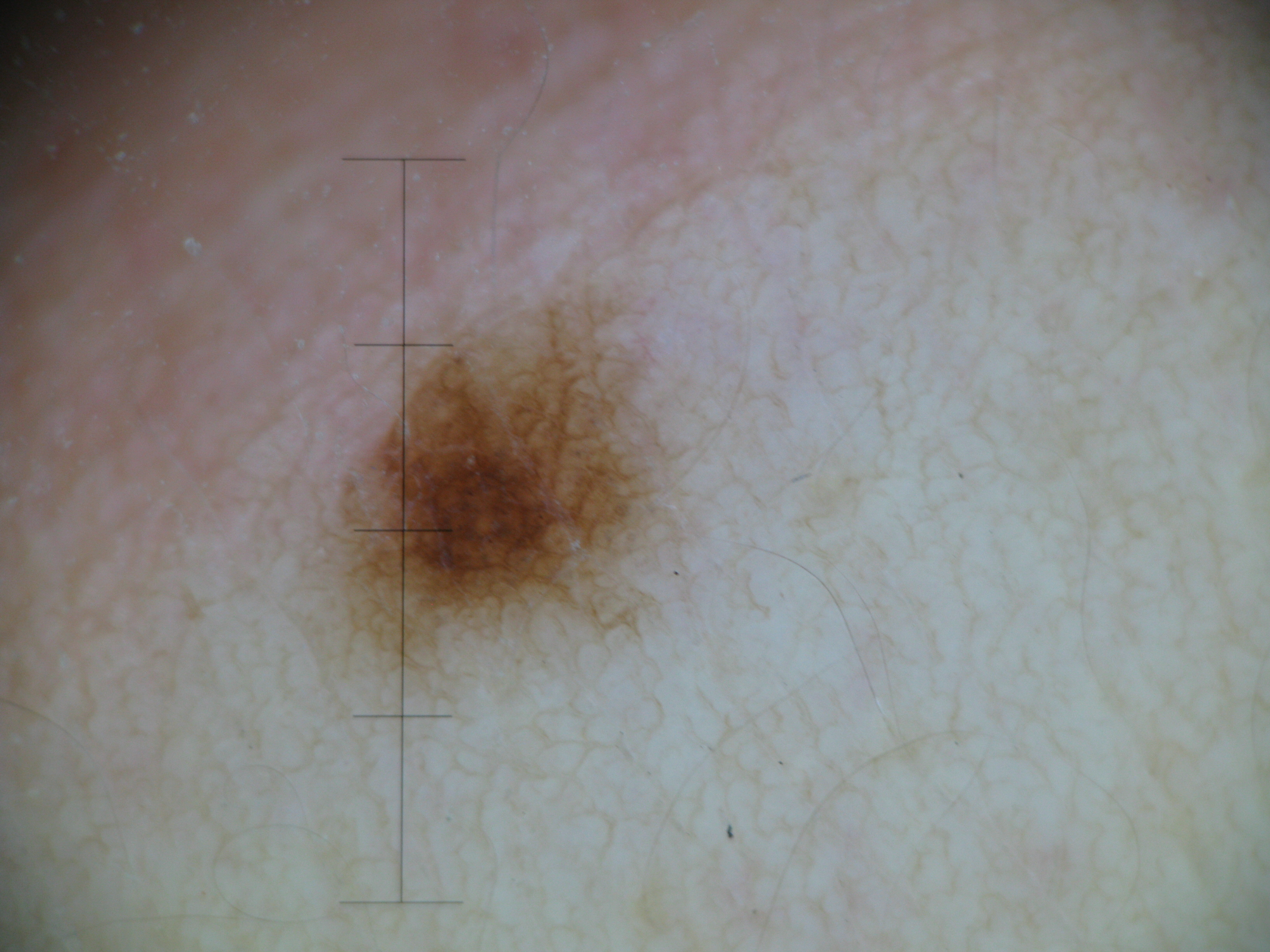Classified as a junctional nevus.